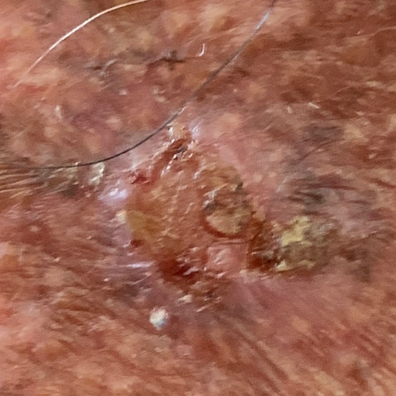| field | value |
|---|---|
| imaging | clinical photo |
| subject | female, 84 years old |
| location | the chest |
| patient-reported symptoms | itching, growth, bleeding, elevation / no change in appearance, no pain |
| pathology | basal cell carcinoma (biopsy-proven) |